A dermoscopic close-up of a skin lesion.
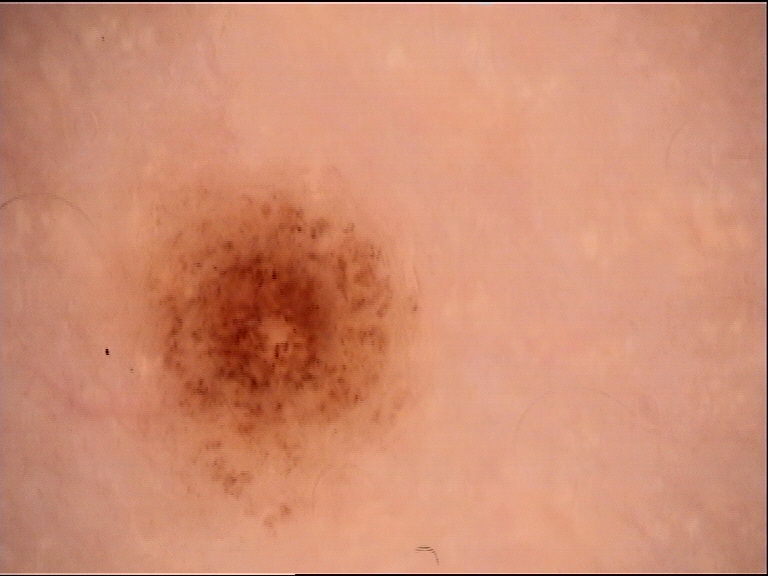Conclusion: The diagnosis was a benign lesion — a dysplastic compound nevus.